Dermoscopy of a skin lesion: 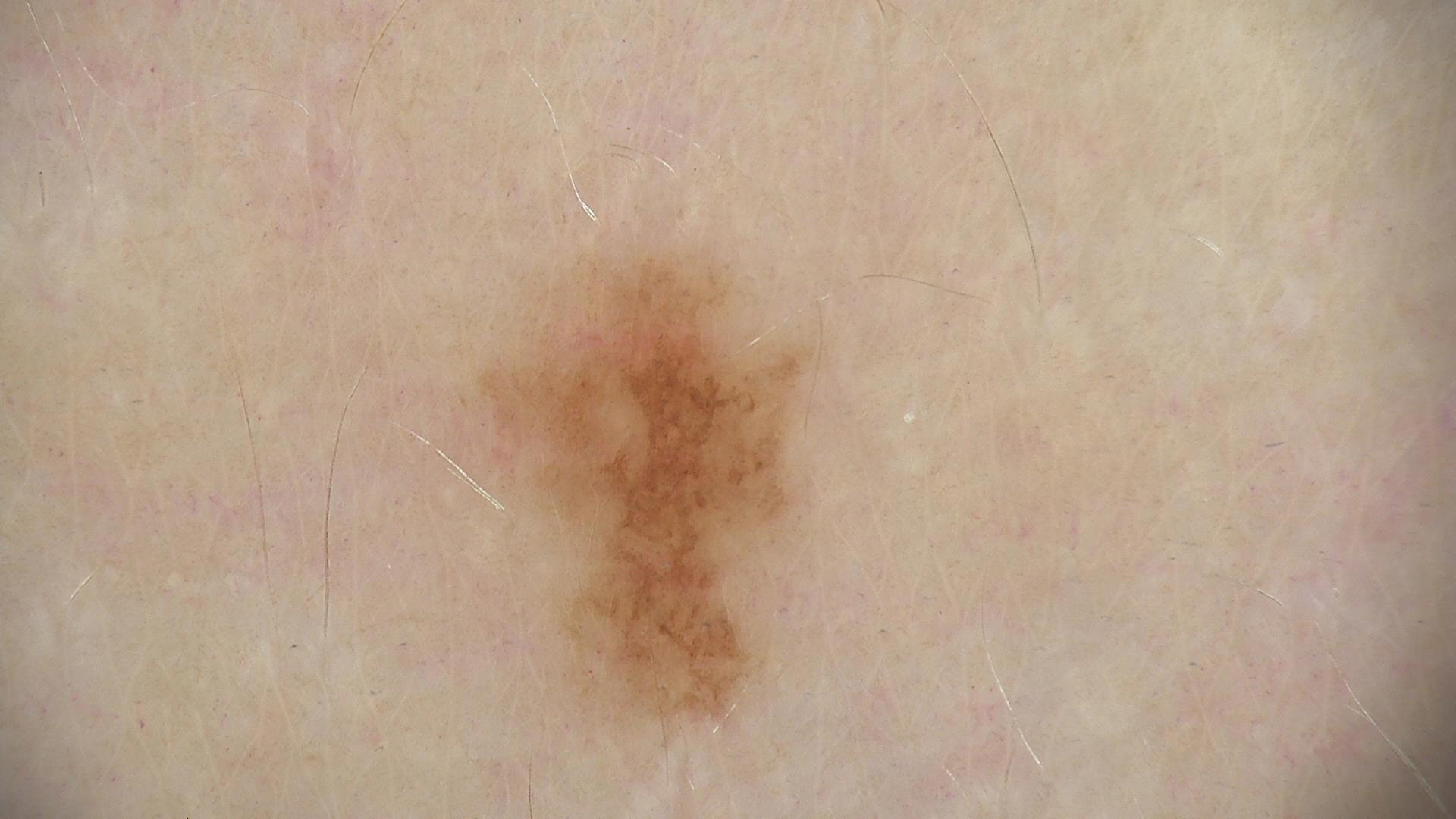Q: What is the diagnosis?
A: dysplastic junctional nevus (expert consensus)